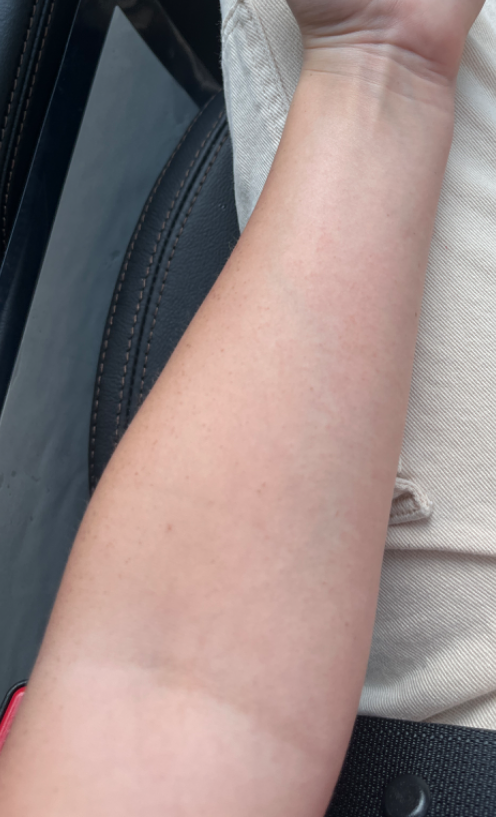Assessment:
The image was not sufficient for the reviewer to characterize the skin condition.
Clinical context:
The photograph was taken at a distance. The contributor is female.